A patient 59 years of age; a clinical close-up photograph of a skin lesion — 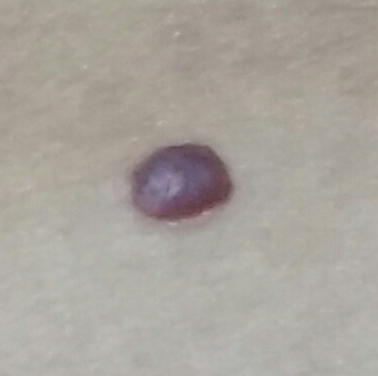Q: Where on the body is the lesion?
A: the abdomen
Q: Any reported symptoms?
A: growth, elevation / no change in appearance, no pain
Q: What is the diagnosis?
A: nevus (clinical consensus)